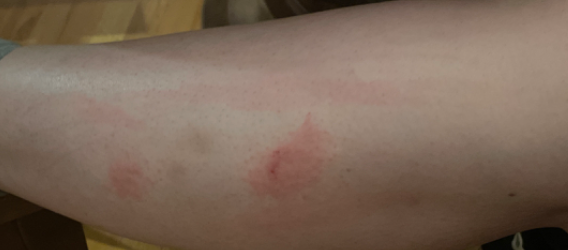The image was not sufficient for the reviewer to characterize the skin condition. The affected area is the leg. This image was taken at a distance. Self-categorized by the patient as a rash. The patient is a female aged 30–39. The patient reports the lesion is raised or bumpy and rough or flaky. The patient reports the condition has been present for one to four weeks. The patient also reports fatigue.